A female subject 58 years old; a moderate number of moles by the patient's own estimate; the patient says their skin tans without first burning; a skin lesion imaged with a dermatoscope — 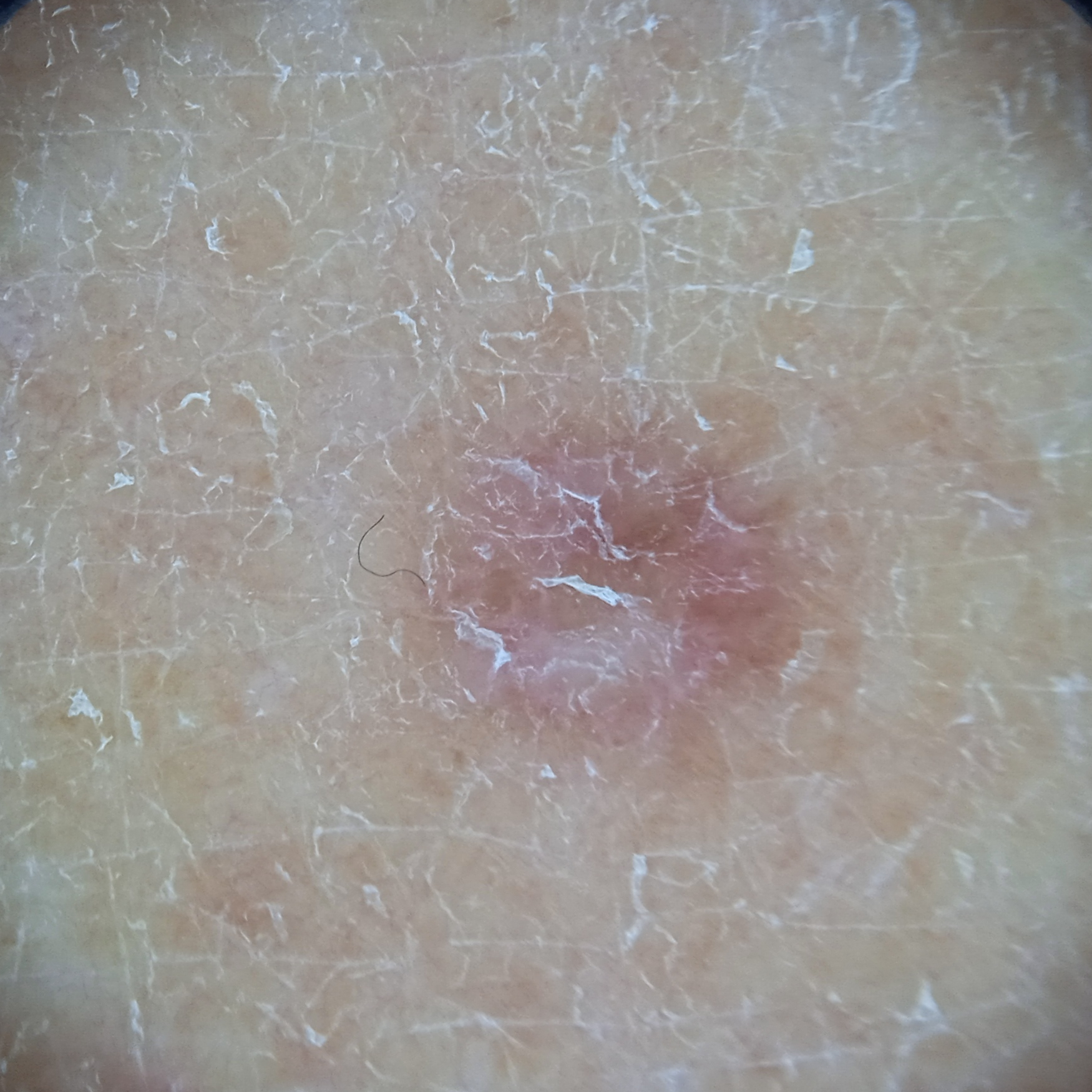Q: Where is the lesion?
A: a leg
Q: How large is the lesion?
A: 5.2 mm
Q: What was the diagnosis?
A: dermatofibroma (dermatologist consensus)